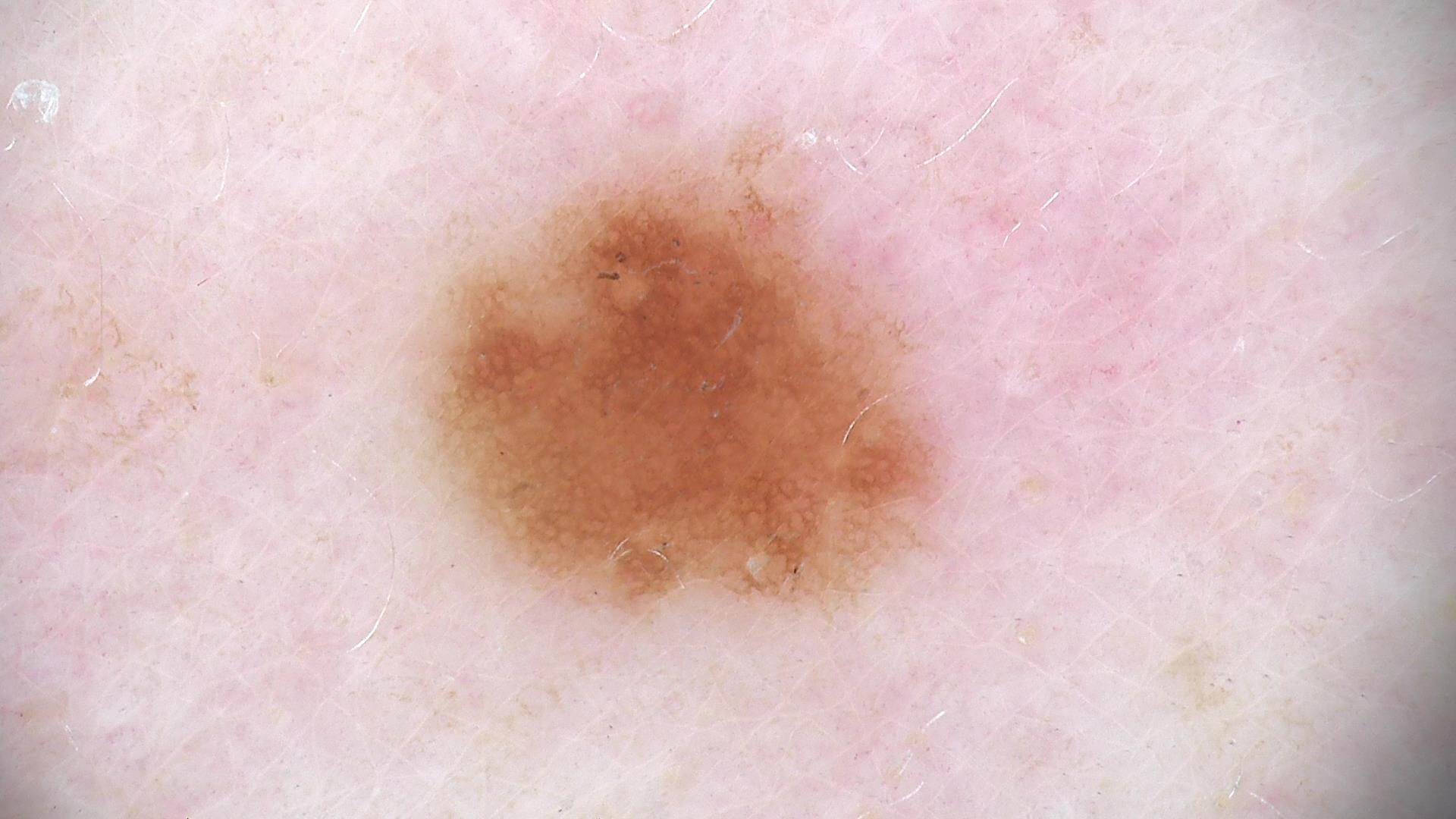Classified as a banal lesion — a junctional nevus.